The lesion involves the arm · male patient, age 70–79 · a close-up photograph: 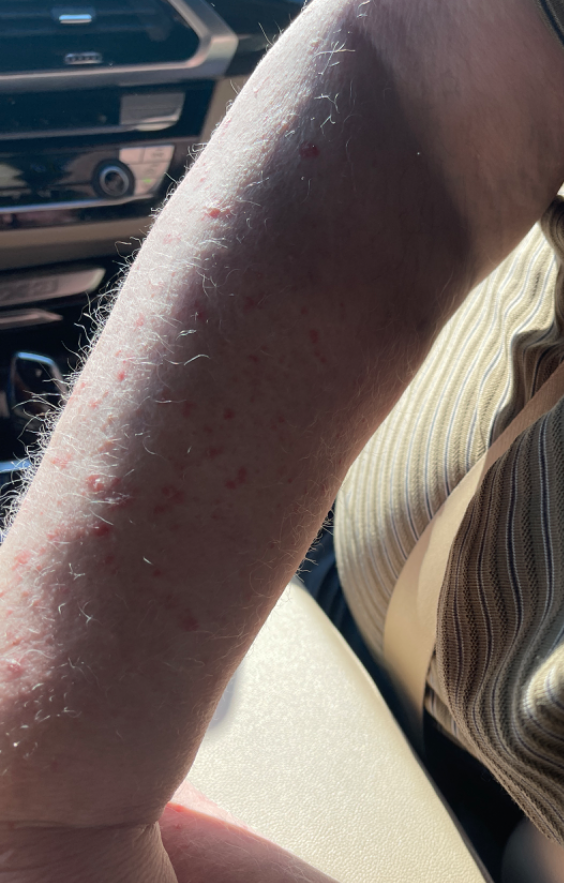diagnostic considerations: the differential, in no particular order, includes Drug Rash, Psoriasis and Eczema.